This is a close-up image, the affected area is the arm — 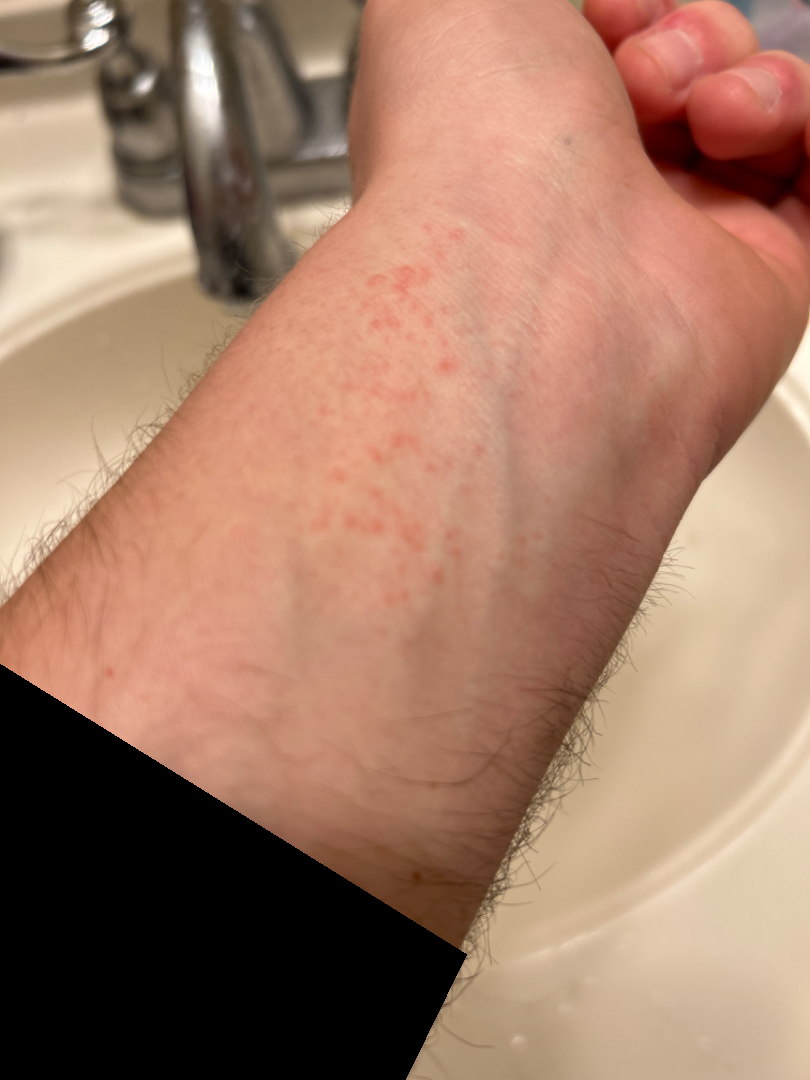Q: What was the assessment?
A: could not be assessed
Q: How does the patient describe it?
A: skin that appeared healthy to them
Q: What symptoms does the patient report?
A: itching
Q: How does the lesion feel?
A: raised or bumpy